A dermoscopy image of a single skin lesion; a male subject approximately 40 years of age:
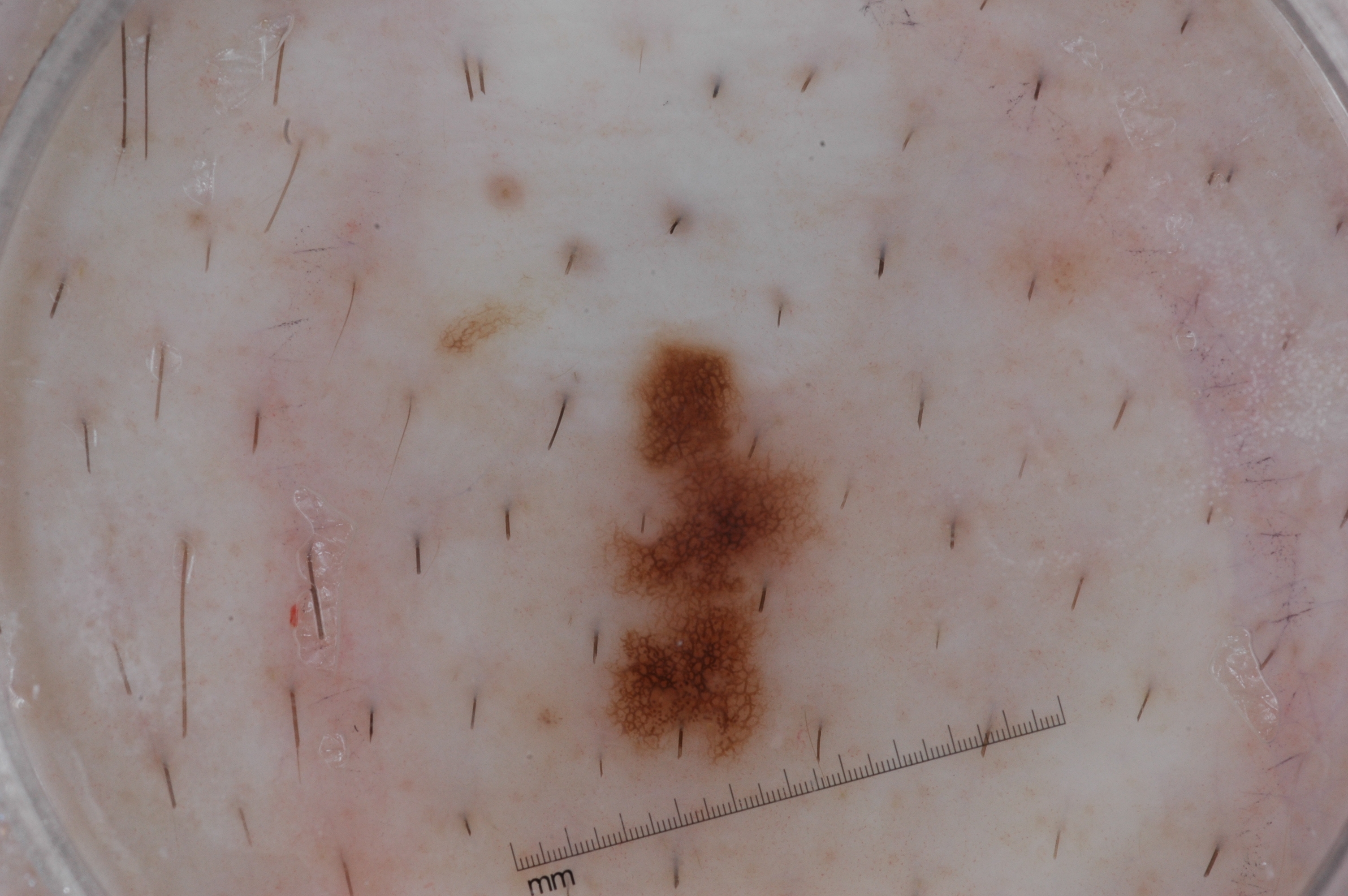Dermoscopically, the lesion shows milia-like cysts and pigment network; no streaks or negative network.
As (left, top, right, bottom), the lesion occupies the region bbox(601, 343, 822, 714).
The lesion occupies roughly 5% of the field.
Diagnosed as a melanocytic nevus, a benign lesion.